The contributor is female, the lesion involves the front of the torso and back of the torso, the photograph is a close-up of the affected area — 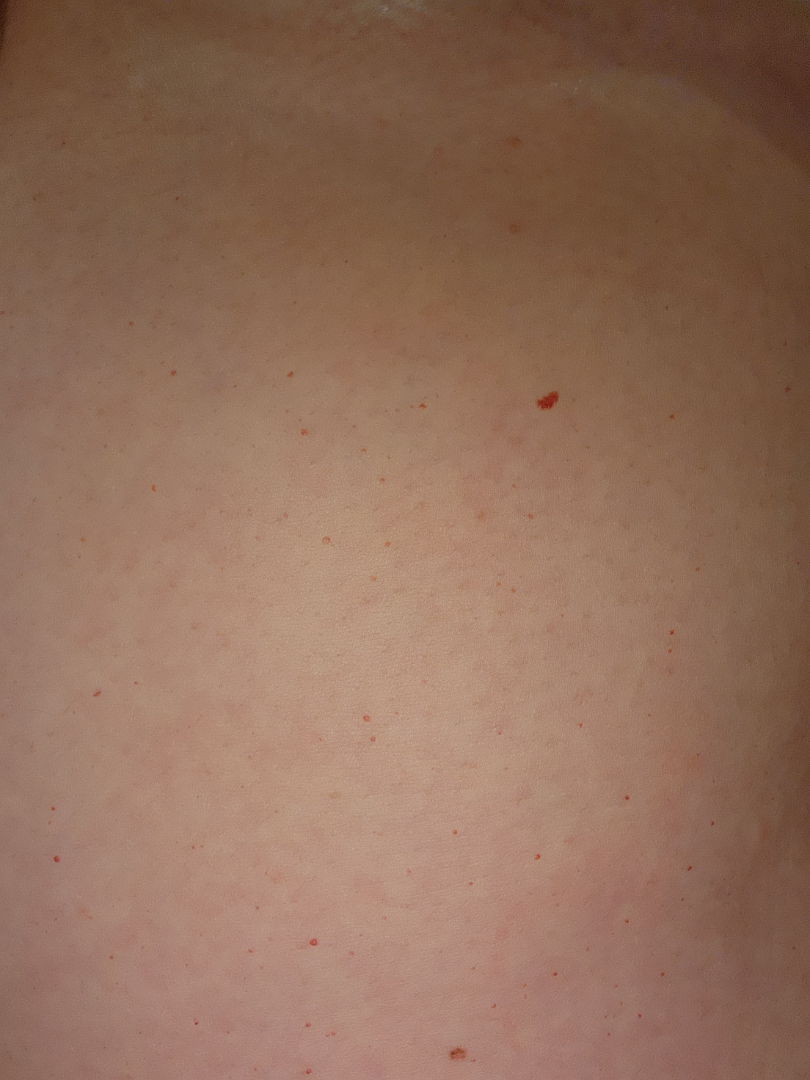The patient also reports fatigue. The patient notes bothersome appearance. The condition has been present for more than five years. The lesion is described as flat. The patient described the issue as a pigmentary problem. On dermatologist assessment of the image: Hemangioma (100%).